A dermoscopic close-up of a skin lesion — 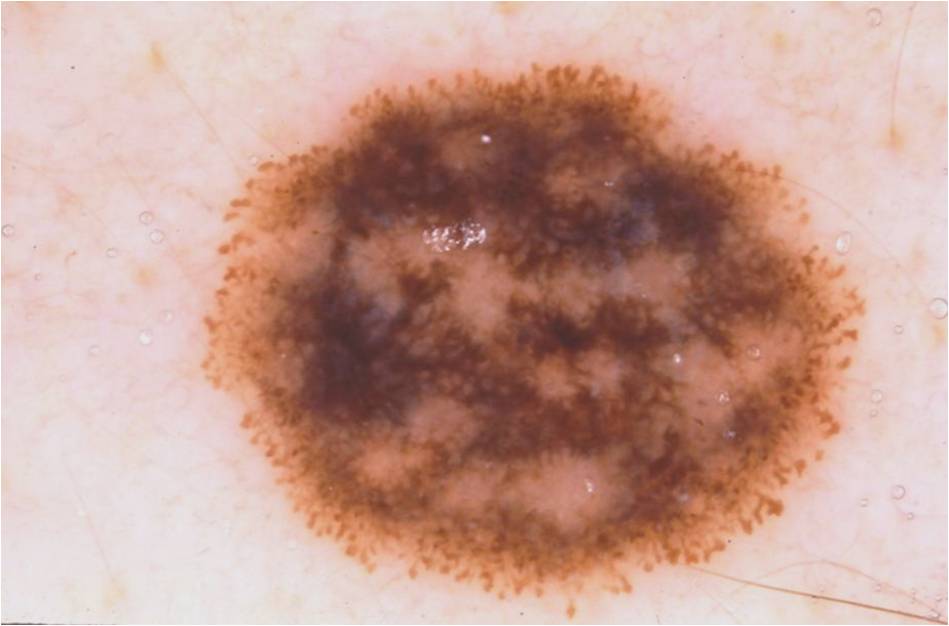Case summary: Dermoscopic assessment notes pigment network, globules, and streaks, with no milia-like cysts or negative network. Lesion location: x1=200, y1=57, x2=864, y2=598. Conclusion: The diagnostic assessment was a melanocytic nevus, a benign skin lesion.